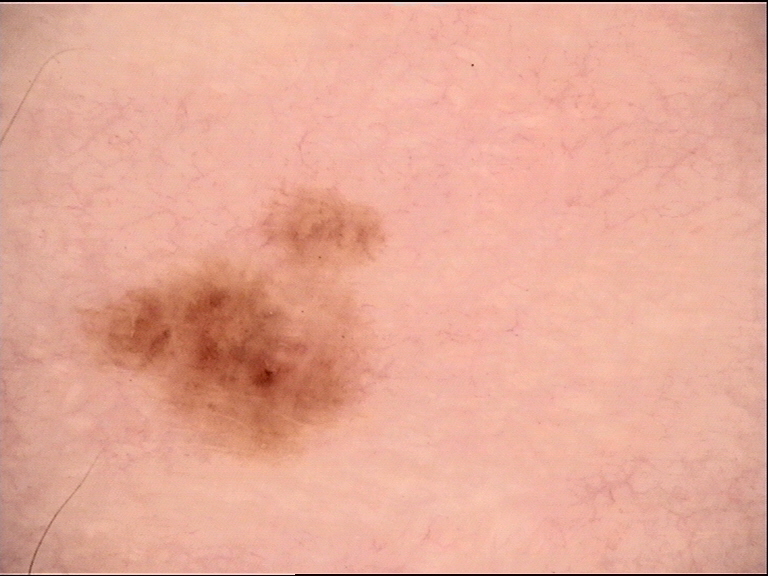Q: What is the diagnosis?
A: dysplastic junctional nevus (expert consensus)